A dermoscopy image of a skin lesion · the patient says their skin reddens with sun exposure · a male patient 83 years of age · acquired for a research image collection, with no referral diagnosis — 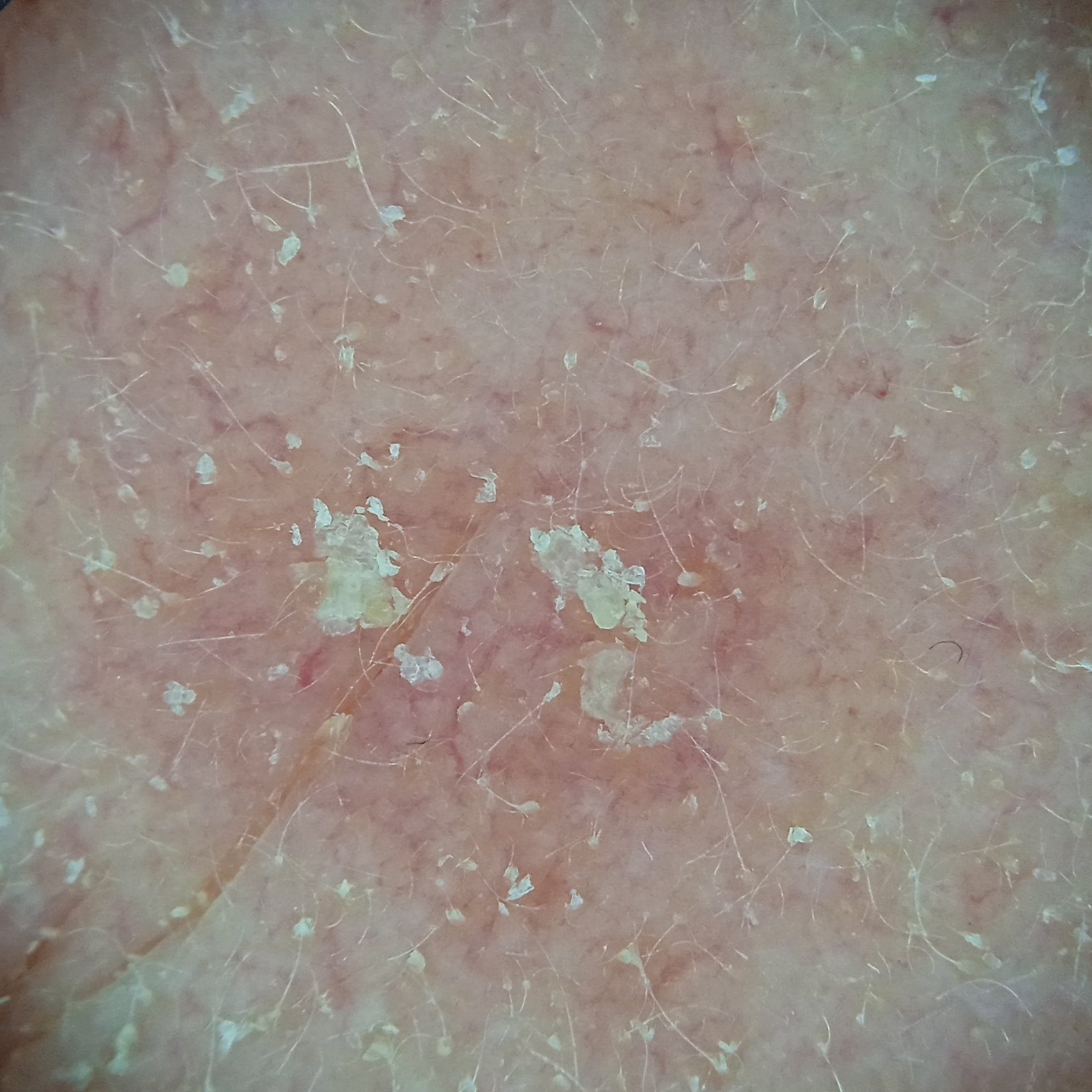- location · the face
- lesion size · 7.5 mm
- diagnostic label · actinic keratosis (dermatologist consensus)